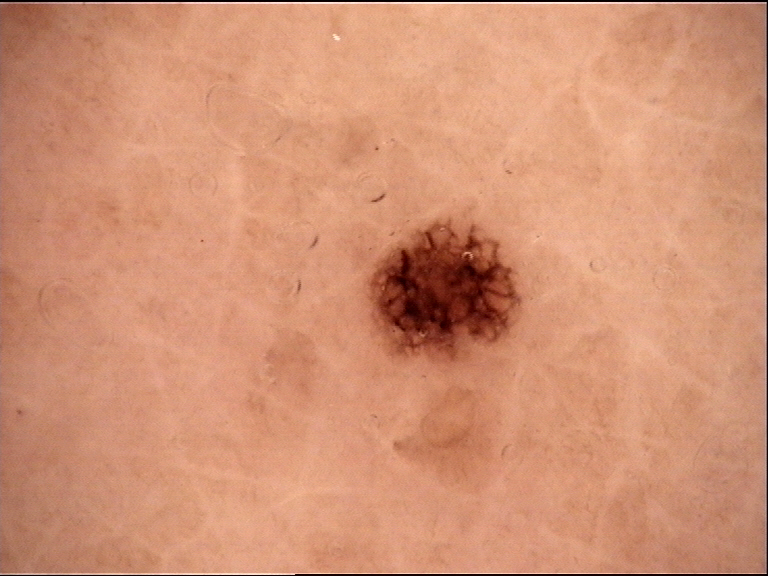Impression: Classified as a dysplastic junctional nevus.